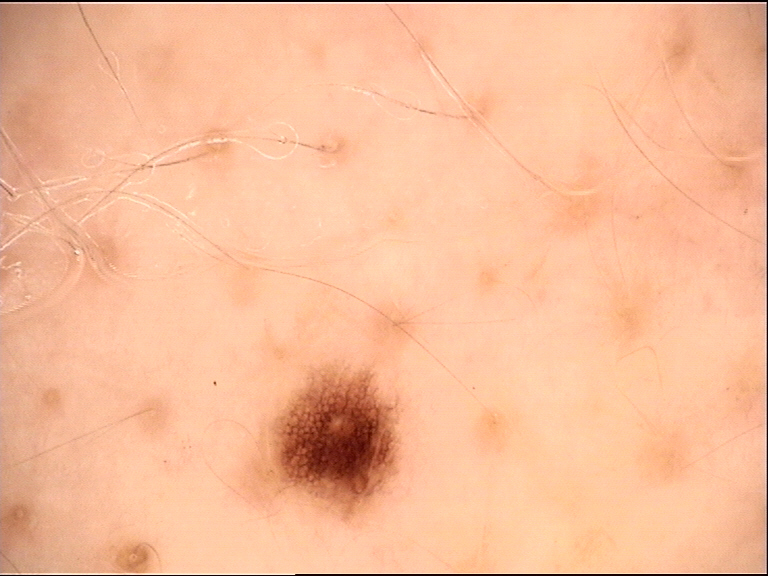imaging: dermatoscopy
diagnosis: dysplastic junctional nevus (expert consensus)